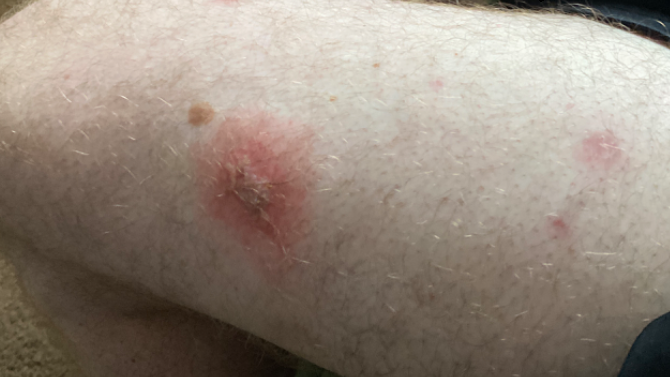{
  "systemic_symptoms": "fever",
  "patient_category": "a rash",
  "shot_type": "at a distance",
  "duration": "less than one week",
  "body_site": "leg",
  "symptoms": [
    "enlargement",
    "bothersome appearance",
    "pain",
    "itching"
  ],
  "differential": {
    "leading": [
      "Impetigo"
    ],
    "considered": [
      "Secondary impetiginization"
    ]
  }
}